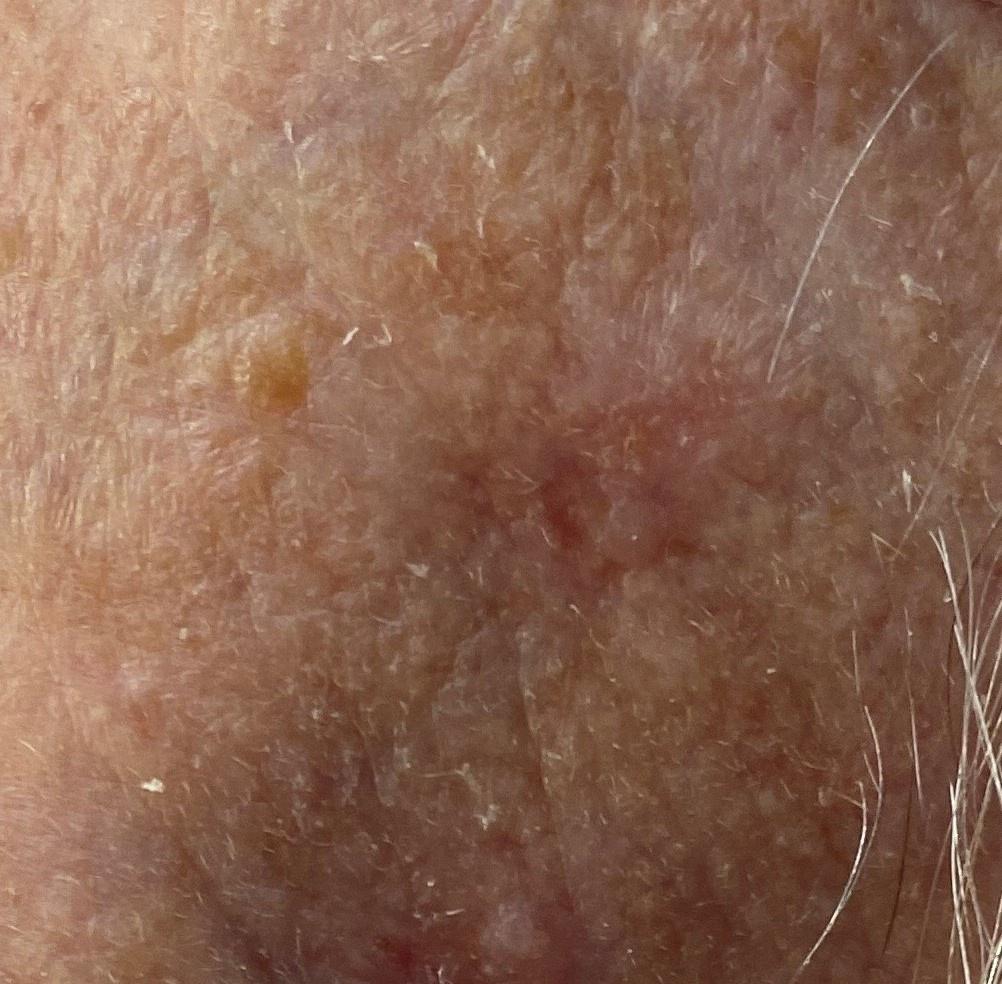Case:
- image type: clinical photo (overview)
- subject: male, approximately 80 years of age
- Fitzpatrick: II
- location: the head or neck
- diagnostic label: Basal cell carcinoma (biopsy-proven)